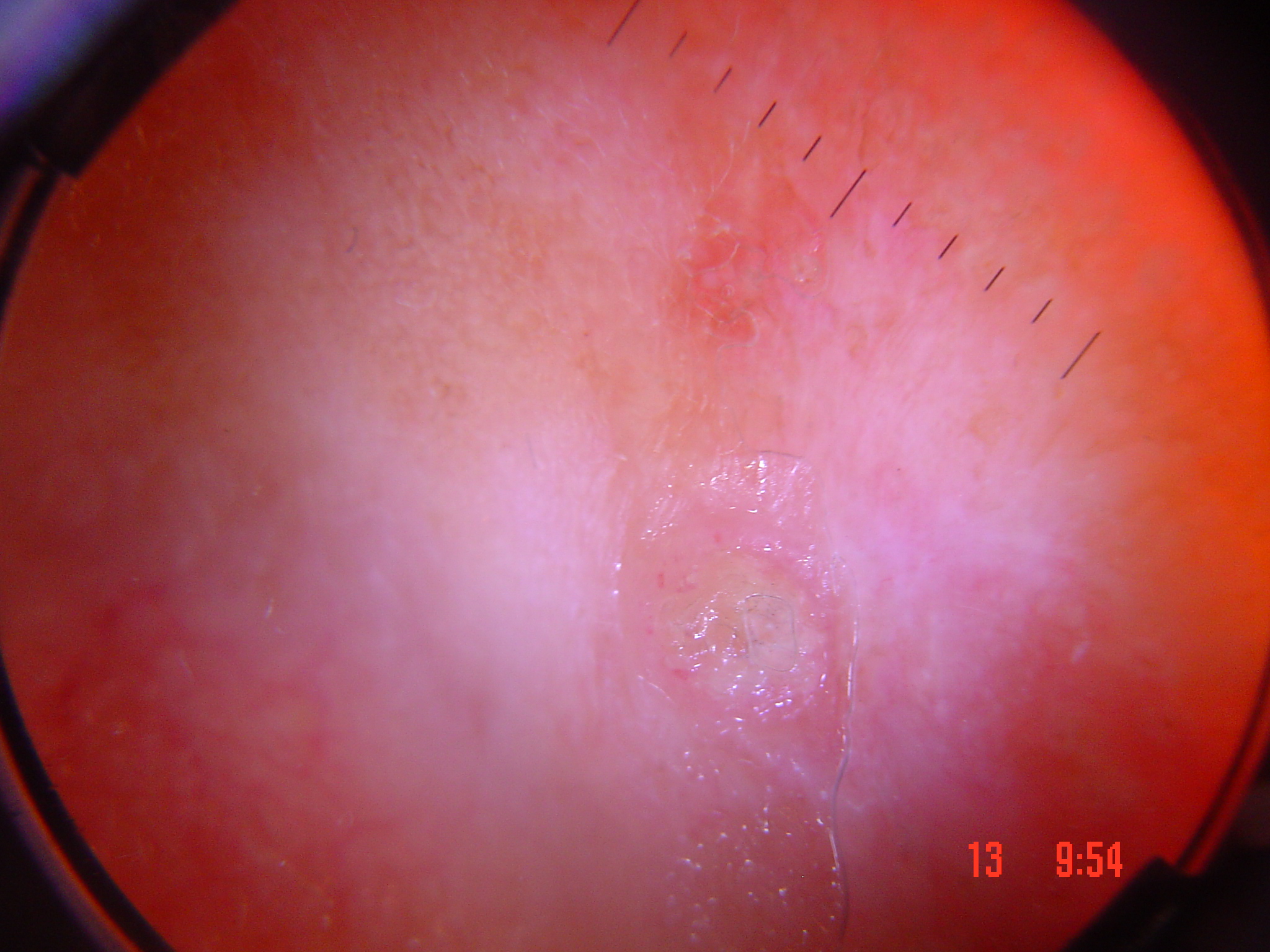A skin lesion imaged with a dermatoscope.
This is a keratinocytic lesion.
Histopathologically confirmed as a malignancy — a squamous cell carcinoma.